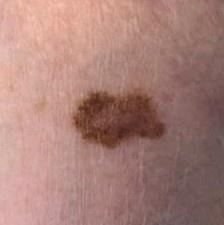<skin_lesion>
<patient>
<age_approx>75</age_approx>
<sex>female</sex>
</patient>
<image>clinical photograph</image>
<lesion_location>
<region>an upper extremity</region>
</lesion_location>
<diagnosis>
<name>Melanoma</name>
<malignancy>malignant</malignancy>
<confirmation>histopathology</confirmation>
</diagnosis>
</skin_lesion>